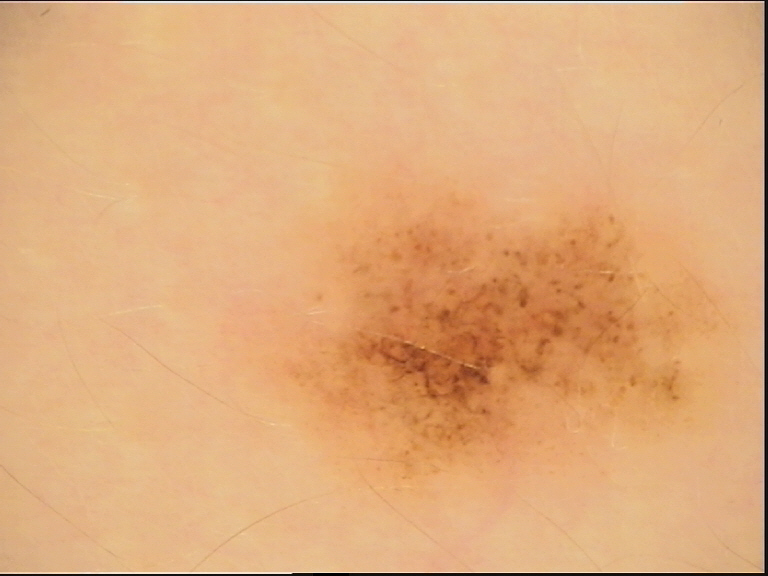image — dermoscopy
class — dysplastic junctional nevus (expert consensus)